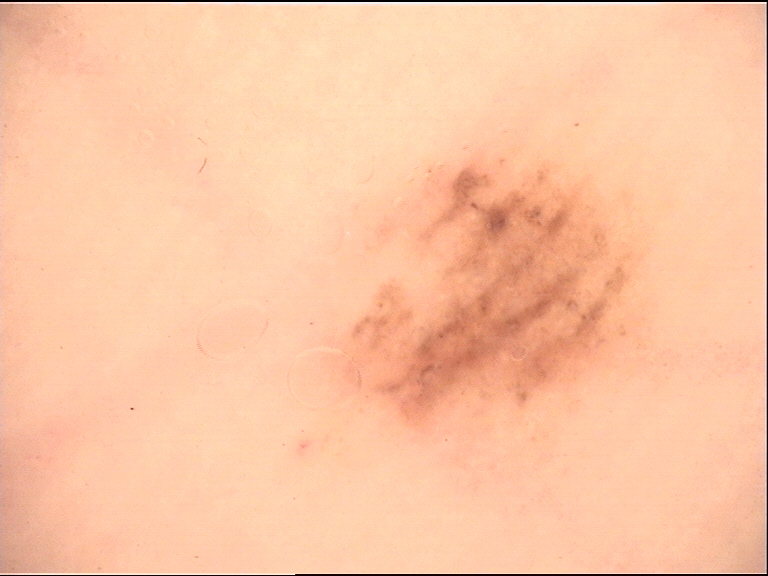  image: dermoscopy
  diagnosis:
    name: acral junctional nevus
    code: ajb
    malignancy: benign
    super_class: melanocytic
    confirmation: expert consensus